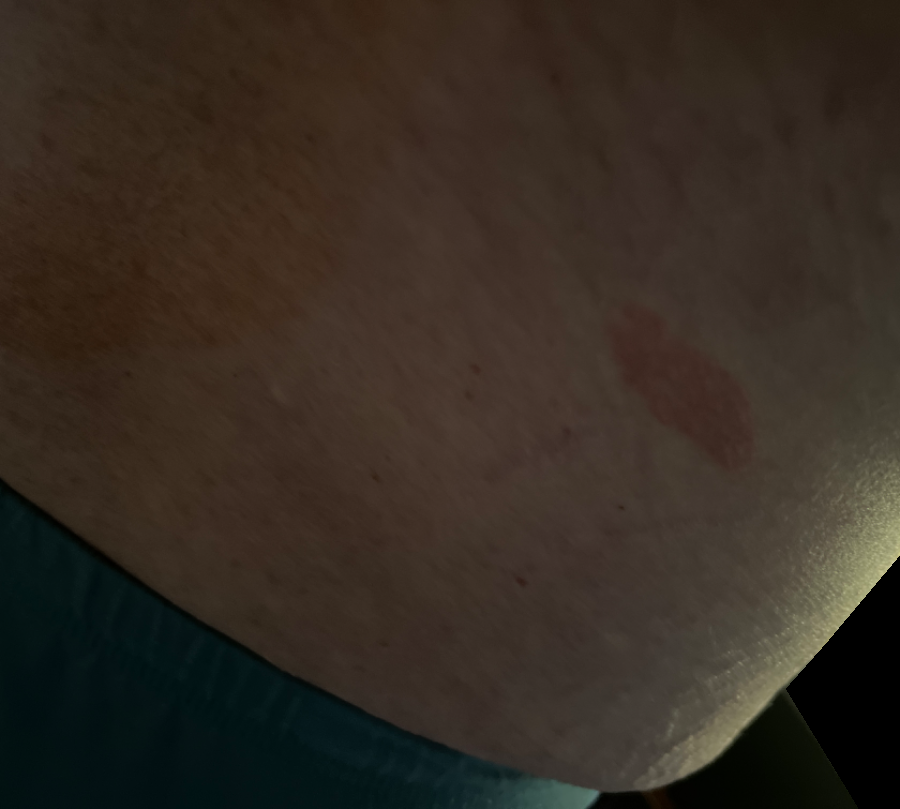This image was taken at an angle. In keeping with Eczema.